A patient 50 years old · a smartphone photograph of a skin lesion — 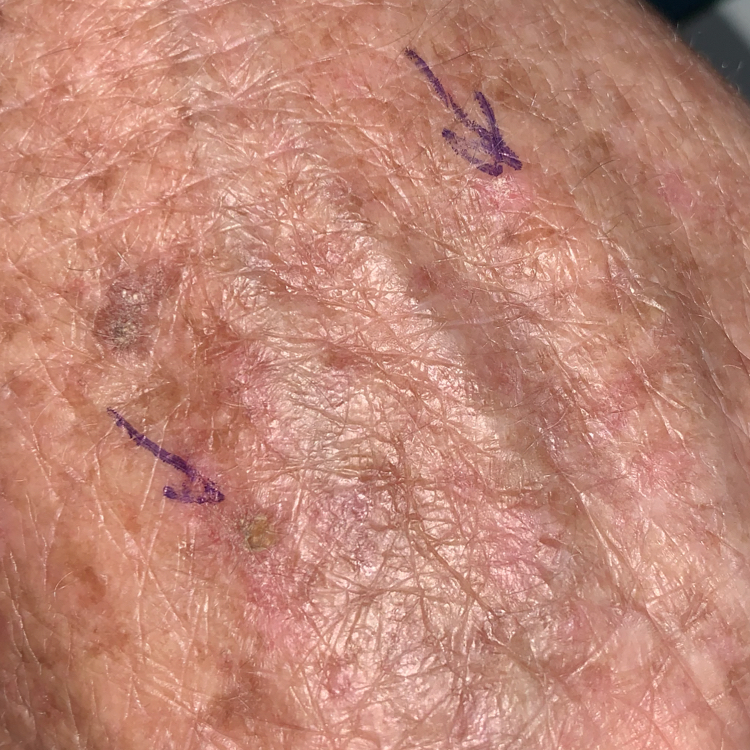Findings: The lesion involves a hand. By the patient's account, the lesion is elevated and itches, but has not changed and does not hurt. Conclusion: Diagnosed by dermatologist consensus as an actinic keratosis.